The subject is a female aged 40–49; the lesion involves the arm, back of the hand and leg; the patient considered this a rash; texture is reported as fluid-filled and raised or bumpy; this is a close-up image; the lesion is associated with itching; no constitutional symptoms were reported; reported duration is less than one week.
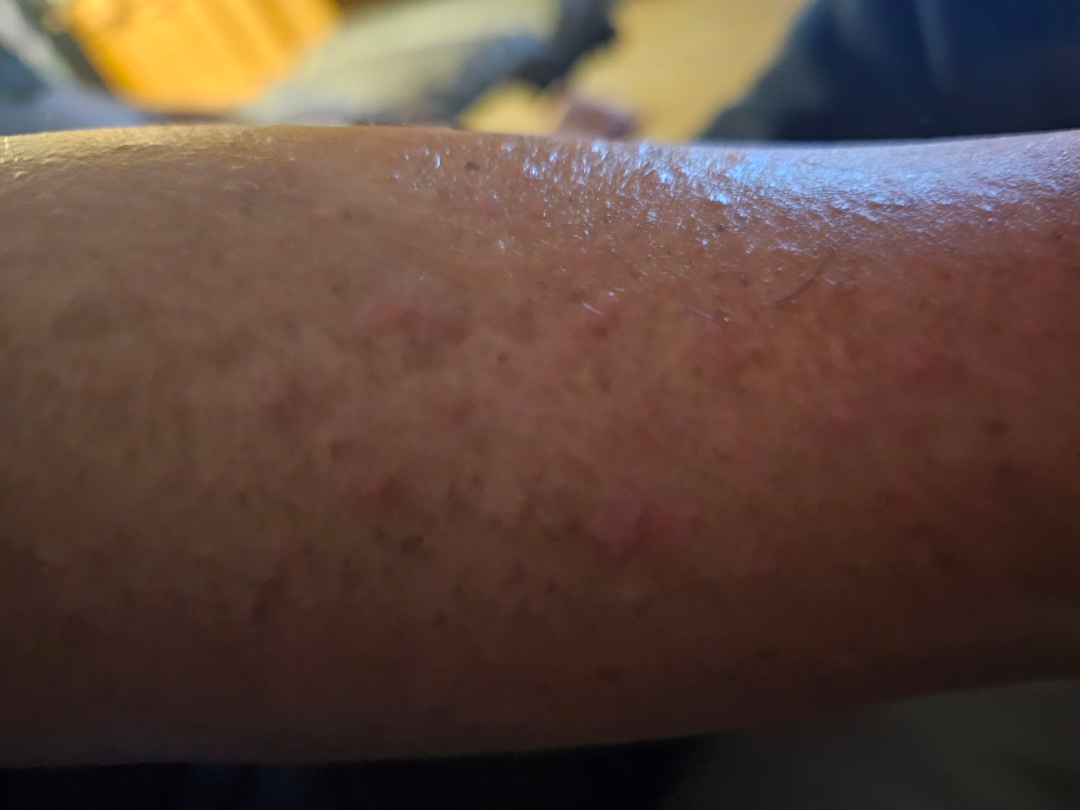differential = in keeping with Stasis Dermatitis.